The lesion involves the arm, leg and back of the hand; a close-up photograph.
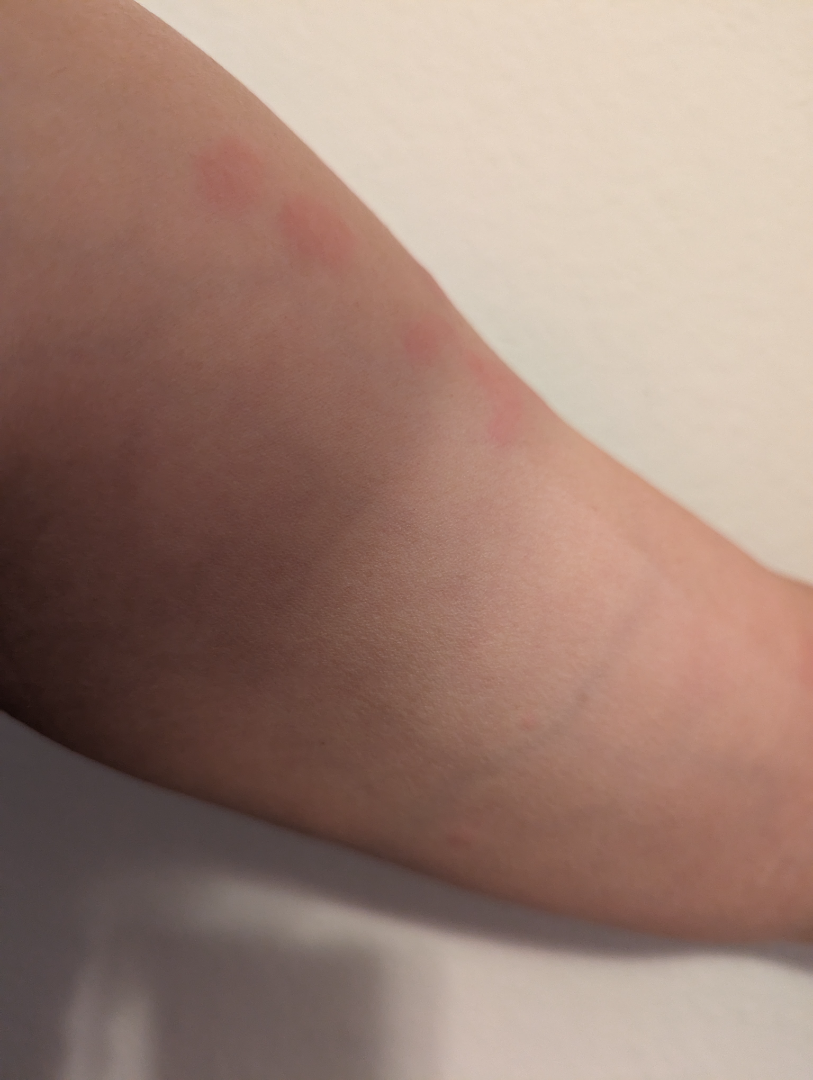Review:
The image was not sufficient for the reviewer to characterize the skin condition.
Patient information:
The contributor reports the condition has been present for one to three months. The contributor reports the lesion is raised or bumpy. The patient considered this skin that appeared healthy to them.